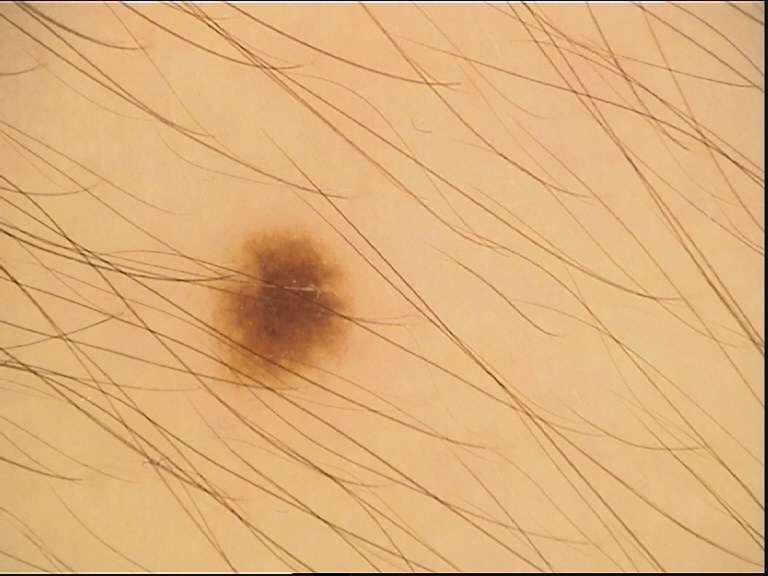Consistent with a benign lesion — a dysplastic junctional nevus.